The patient is 18–29, female · the photo was captured at an angle · located on the head or neck and arm — 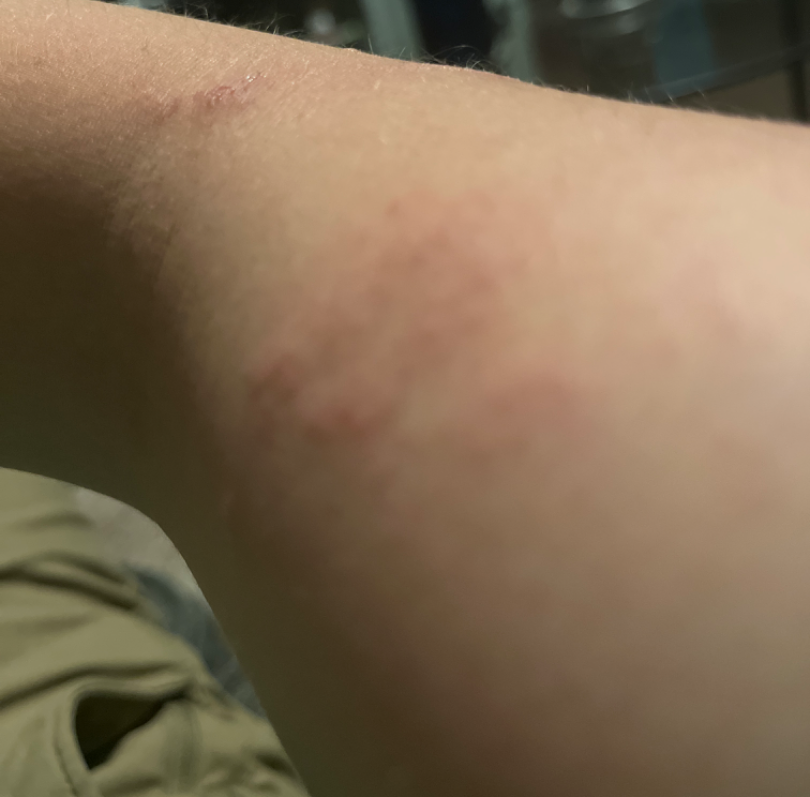<case>
  <assessment>unable to determine</assessment>
  <symptoms>itching</symptoms>
</case>